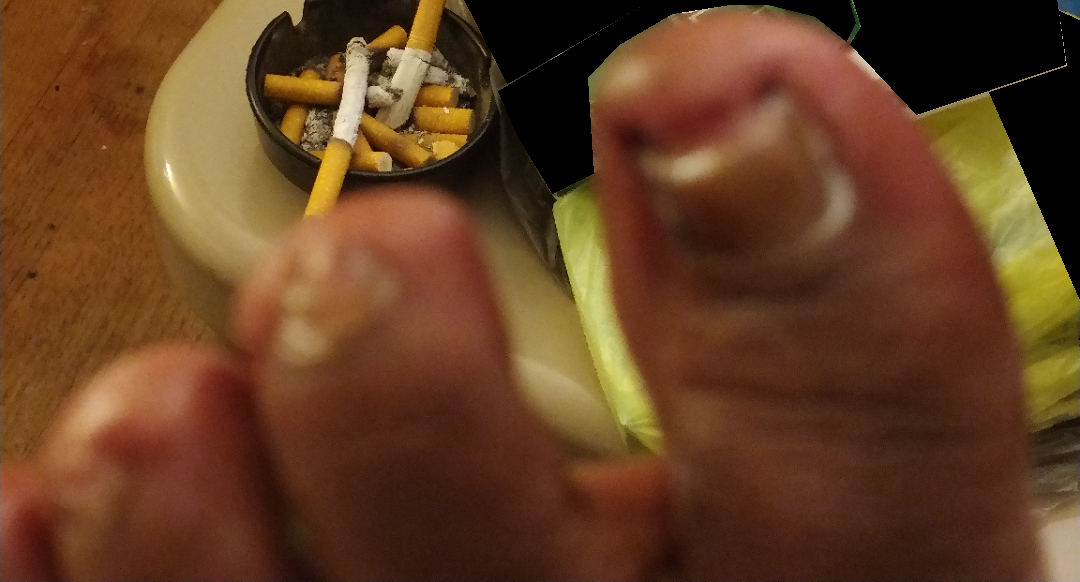- surface texture · fluid-filled
- self-categorized as · a nail problem
- framing · at an angle
- lesion symptoms · bothersome appearance, bleeding, pain and darkening
- constitutional symptoms · mouth sores, joint pain and fatigue
- affected area · top or side of the foot
- contributor · female, age 50–59
- duration · more than one year
- clinical impression · Pincer nail deformity (primary)